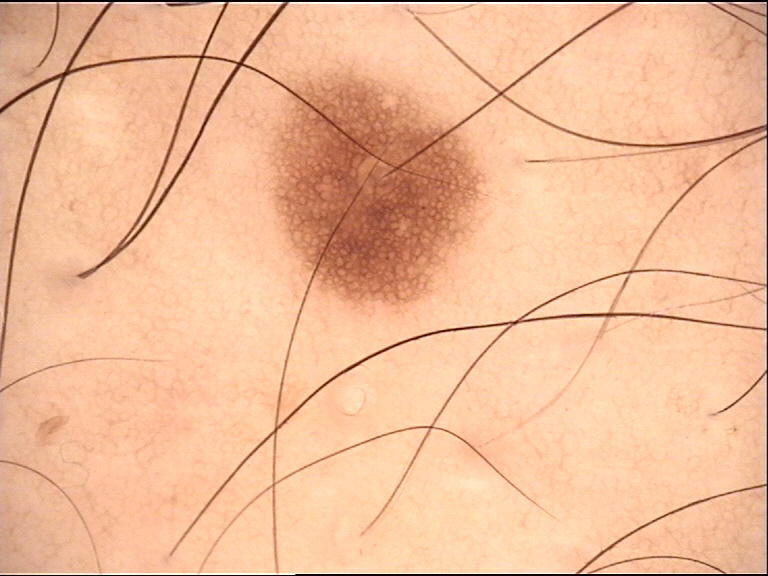diagnostic label = junctional nevus (expert consensus)